A female patient aged 58-62; a dermatoscopic image of a skin lesion: 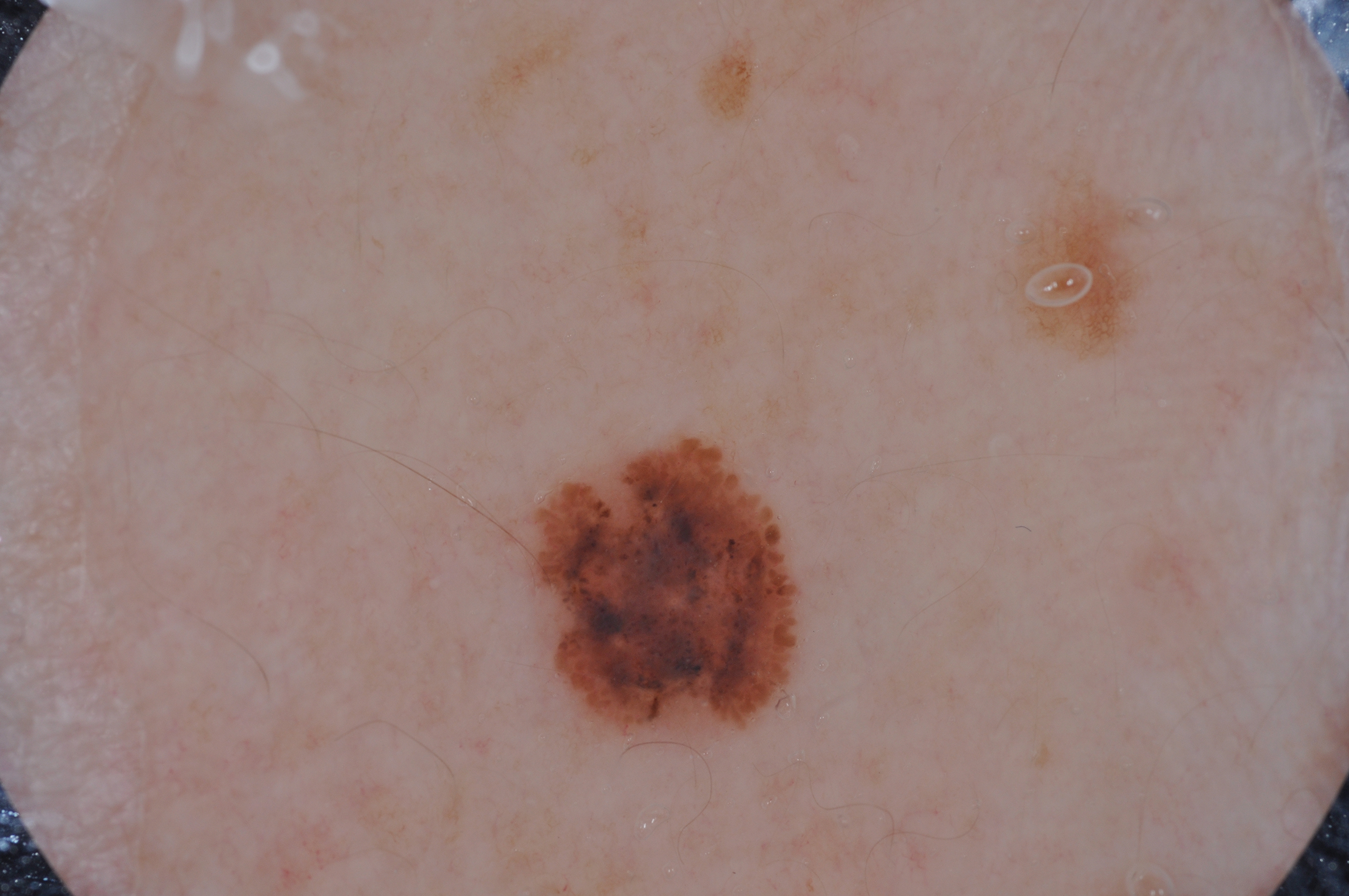Lesion location: left=527, top=441, right=801, bottom=735. Dermoscopic examination shows streaks; no milia-like cysts, negative network, or pigment network. The biopsy diagnosis was a melanoma, a malignant skin lesion.